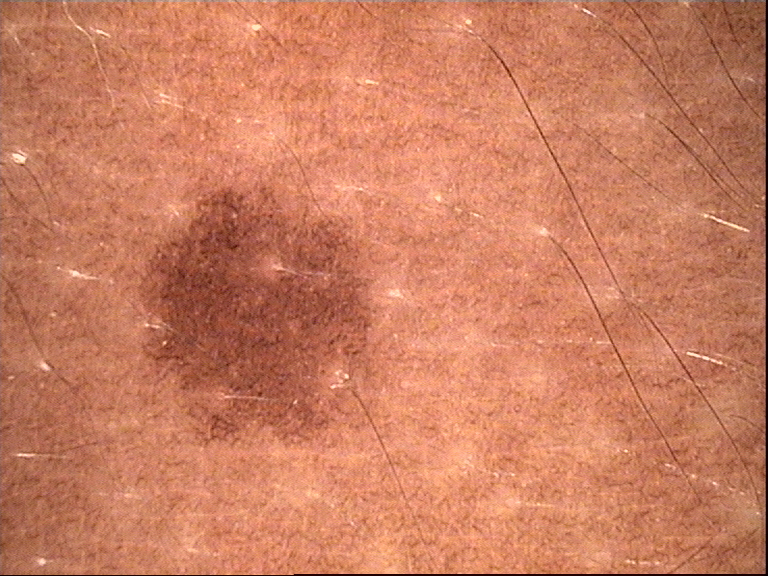class = junctional nevus (expert consensus)